The subject is a male aged 48 to 52; a dermoscopic view of a skin lesion — 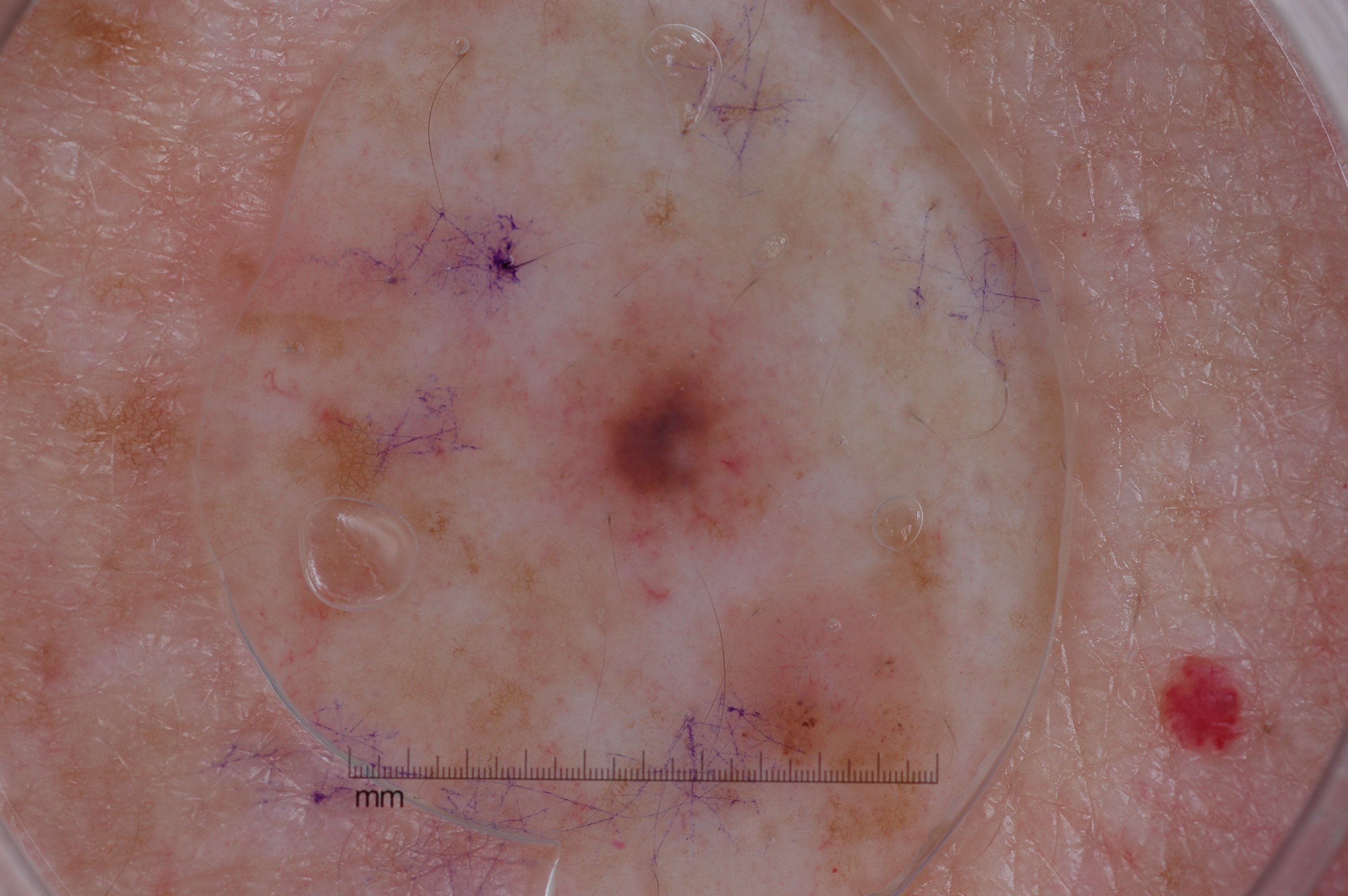Dermoscopically, the lesion shows milia-like cysts. The lesion spans bbox(537, 298, 795, 575). Diagnosed as a melanocytic nevus.